The contributor is 60–69, female; the photograph was taken at a distance; the top or side of the foot, arm, sole of the foot and leg are involved: 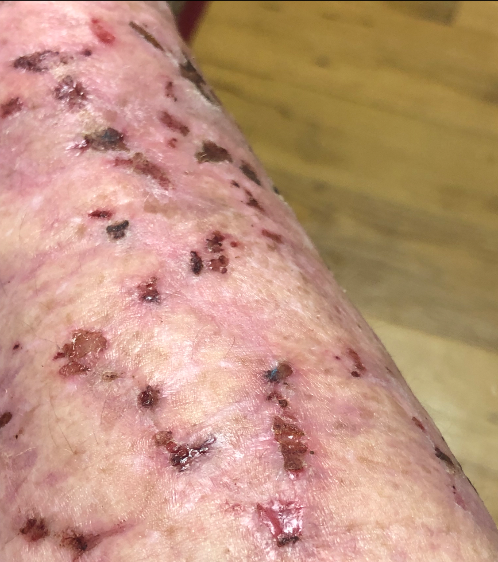The patient also reports mouth sores, fatigue and joint pain.
The contributor reports the lesion is raised or bumpy and rough or flaky.
Reported lesion symptoms include bothersome appearance, darkening, bleeding, enlargement and pain.
The contributor reports the condition has been present for more than one year.
On remote dermatologist review, the impression is varicose vein.